The patient reports the lesion is raised or bumpy and fluid-filled · the photograph was taken at an angle · skin tone: Fitzpatrick IV; human graders estimated a MST of 3 · located on the arm, back of the hand, top or side of the foot, leg and front of the torso · male contributor, age 18–29 · present for one to four weeks · reported lesion symptoms include bothersome appearance, itching and burning · self-categorized by the patient as a rash · no associated systemic symptoms reported.
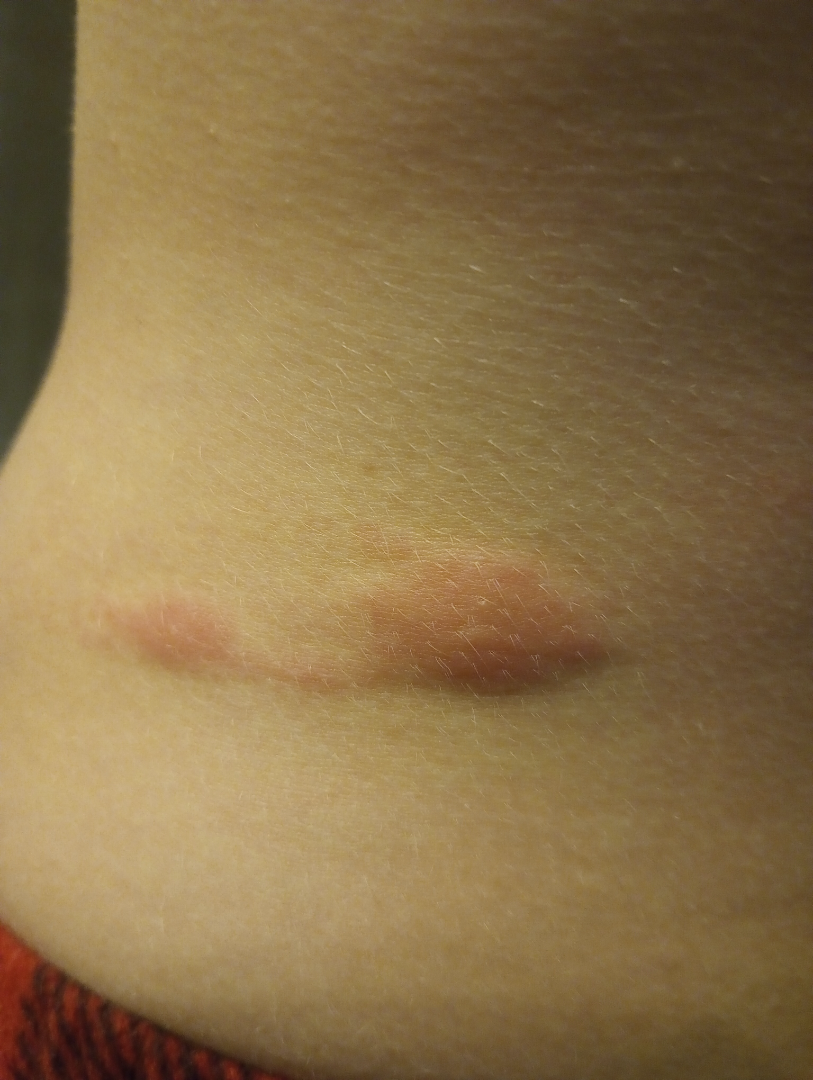differential:
  tied_lead:
    - Allergic Contact Dermatitis
    - Irritant Contact Dermatitis